A female subject aged 73-77; a dermatoscopic image of a skin lesion.
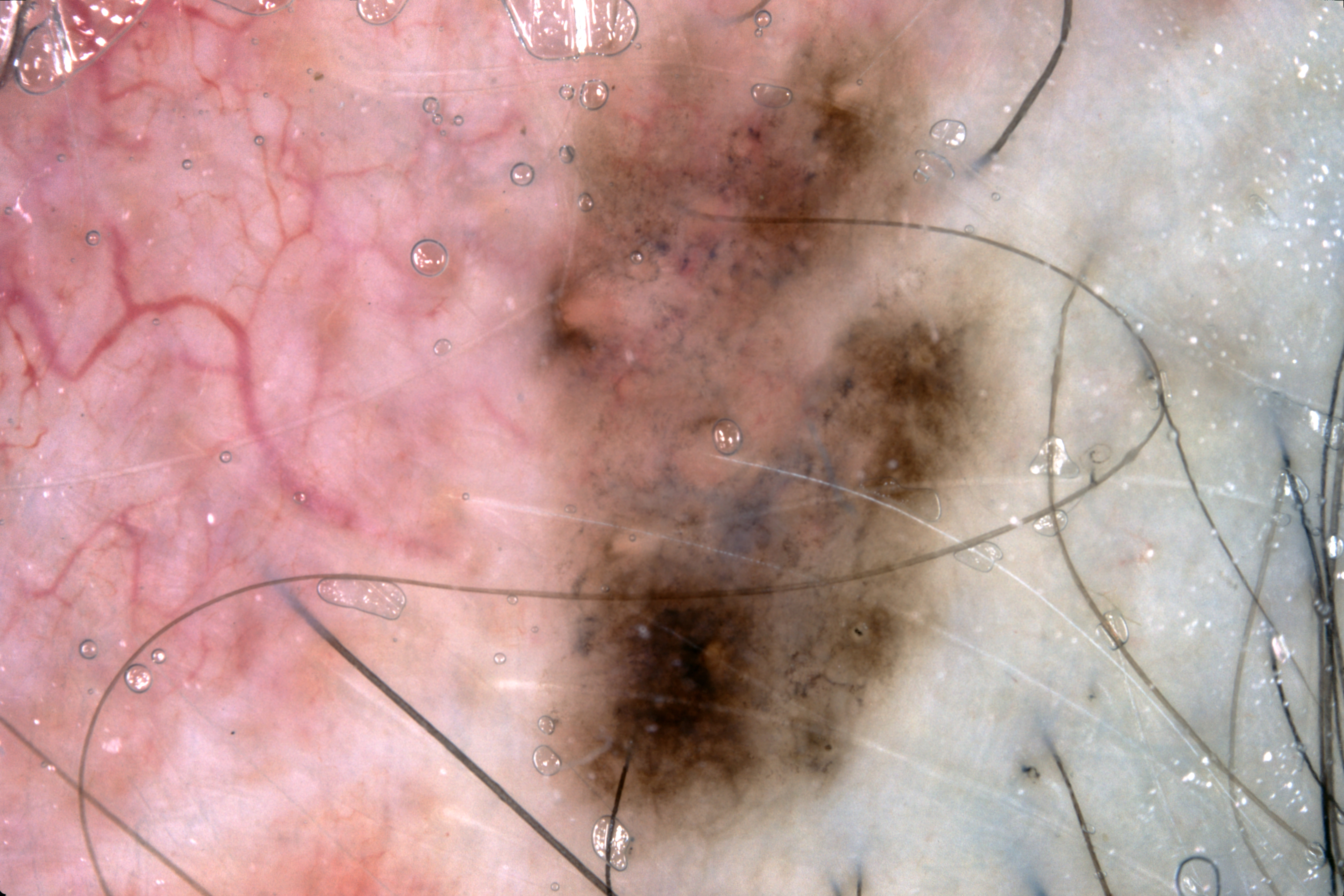dermoscopic pattern — pigment network; absent: streaks, milia-like cysts, and negative network
extent — large
lesion bbox — x1=472 y1=2 x2=1045 y2=894
diagnosis — a melanoma